A skin lesion imaged with a dermatoscope; the patient is a female aged 53-57.
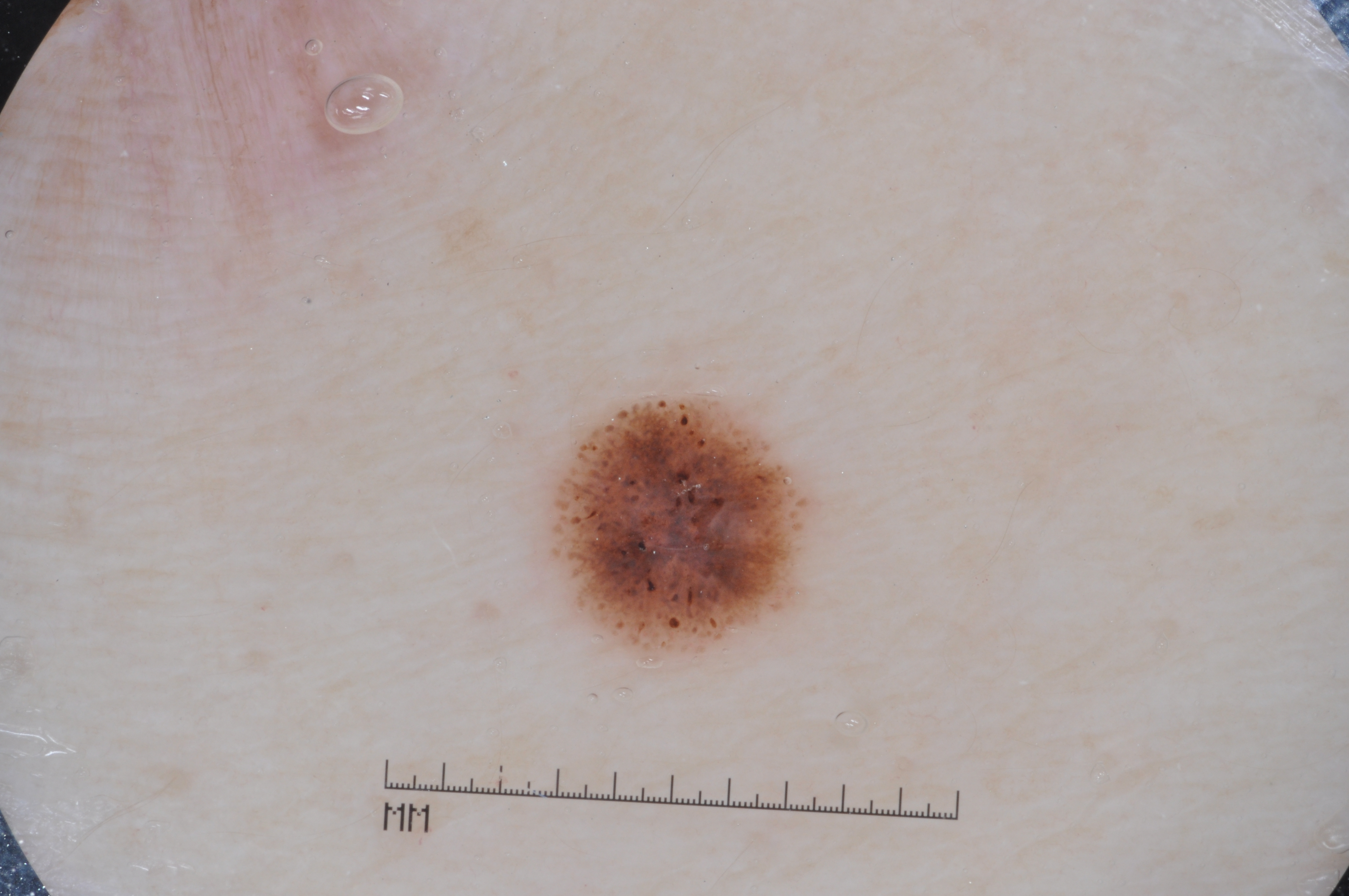• extent · ~4% of the field
• dermoscopic pattern · pigment network; absent: negative network, streaks, and milia-like cysts
• lesion bbox · 548 399 811 658
• diagnostic label · a melanoma, a malignant skin lesion